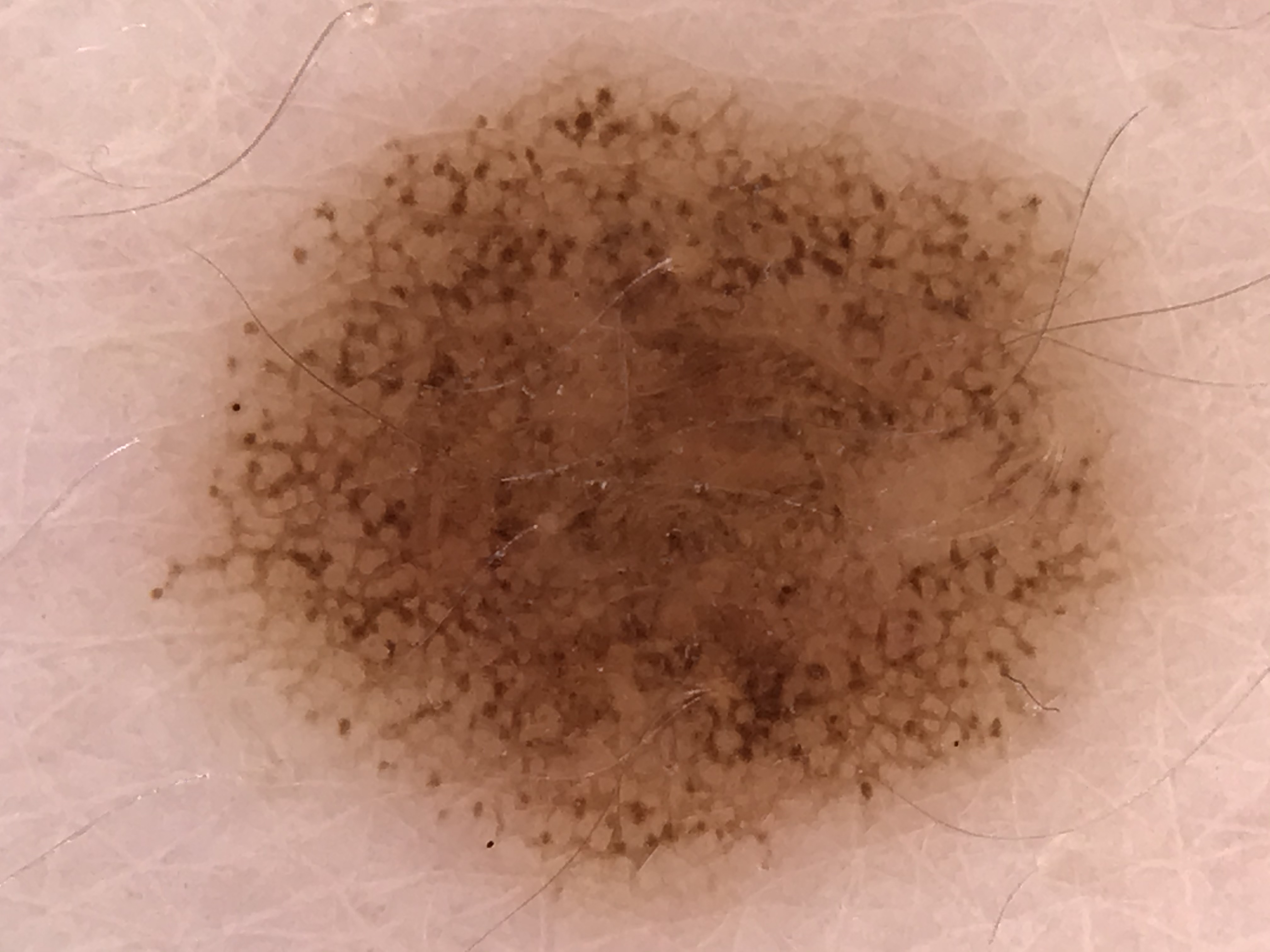{
  "image": "dermatoscopy",
  "diagnosis": {
    "name": "dysplastic junctional nevus",
    "code": "jd",
    "malignancy": "benign",
    "super_class": "melanocytic",
    "confirmation": "expert consensus"
  }
}